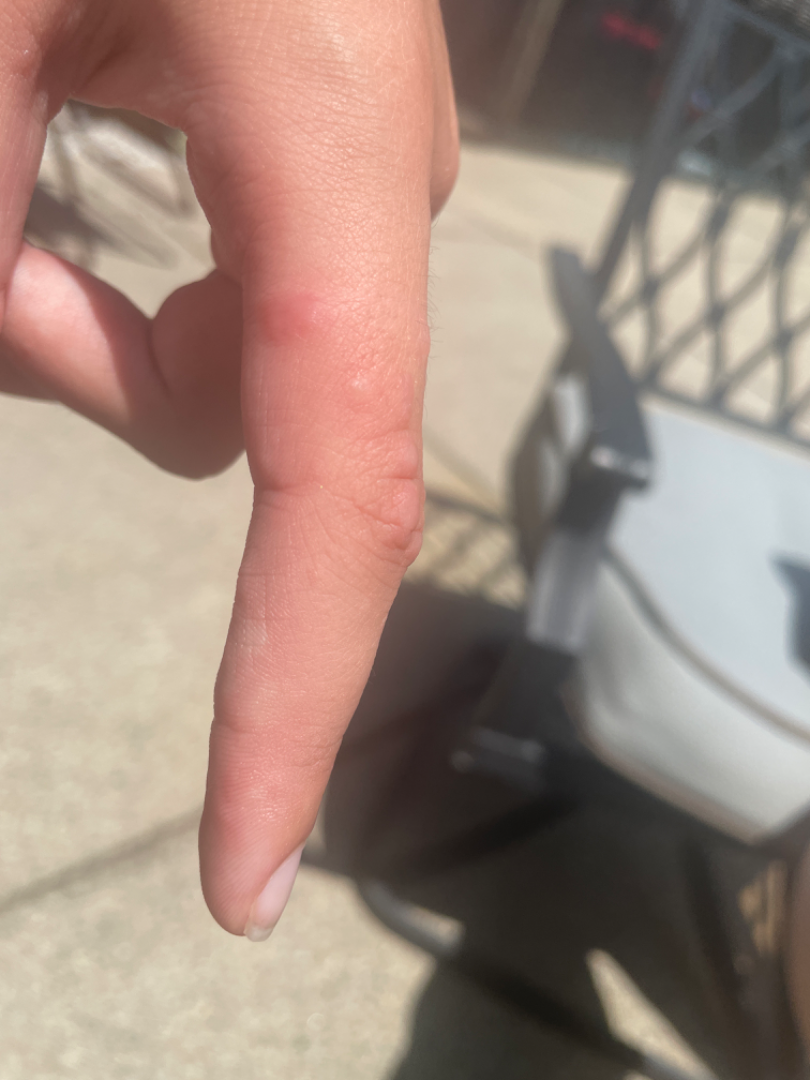On remote review of the image, the impression was split between Rheumatoid nodule and Granuloma annulare.